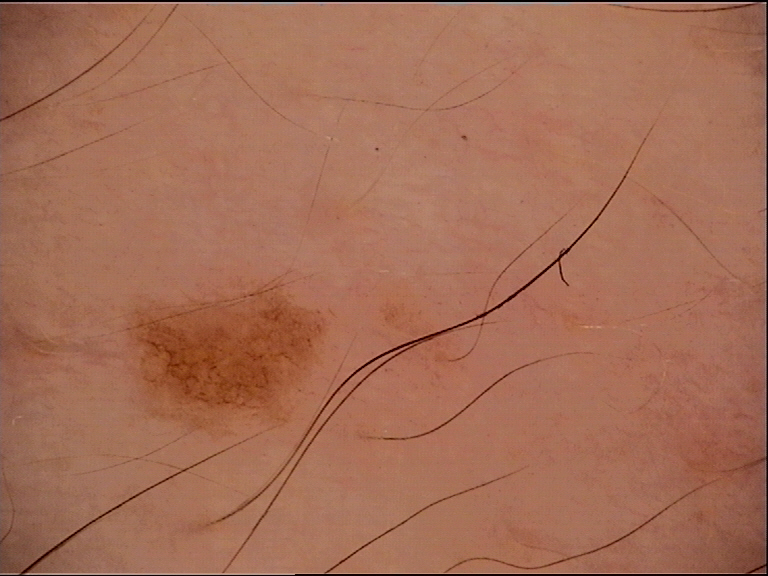The diagnosis was a dysplastic junctional nevus.